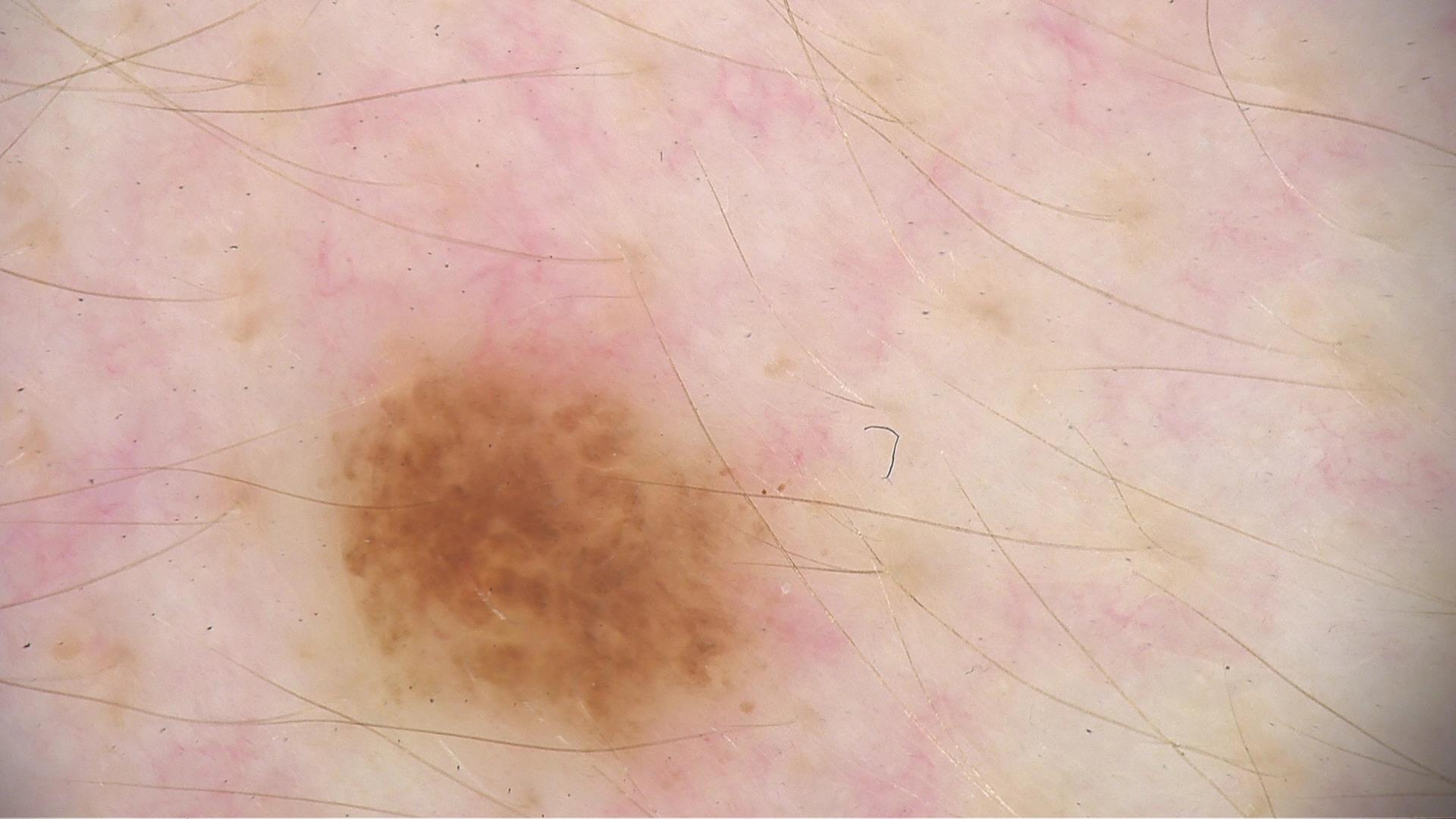The diagnostic label was a dysplastic junctional nevus.